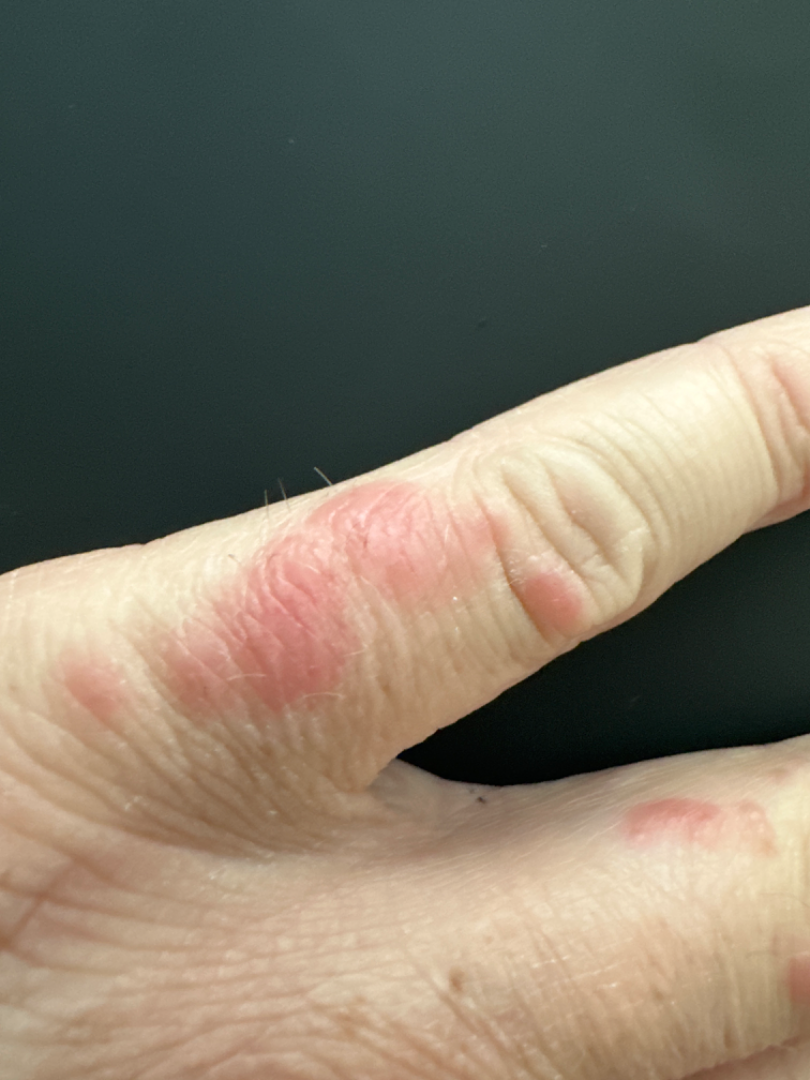{
  "differential": [
    "Eczema",
    "Allergic Contact Dermatitis"
  ]
}